A dermoscopic close-up of a skin lesion · a male patient, in their 80s — 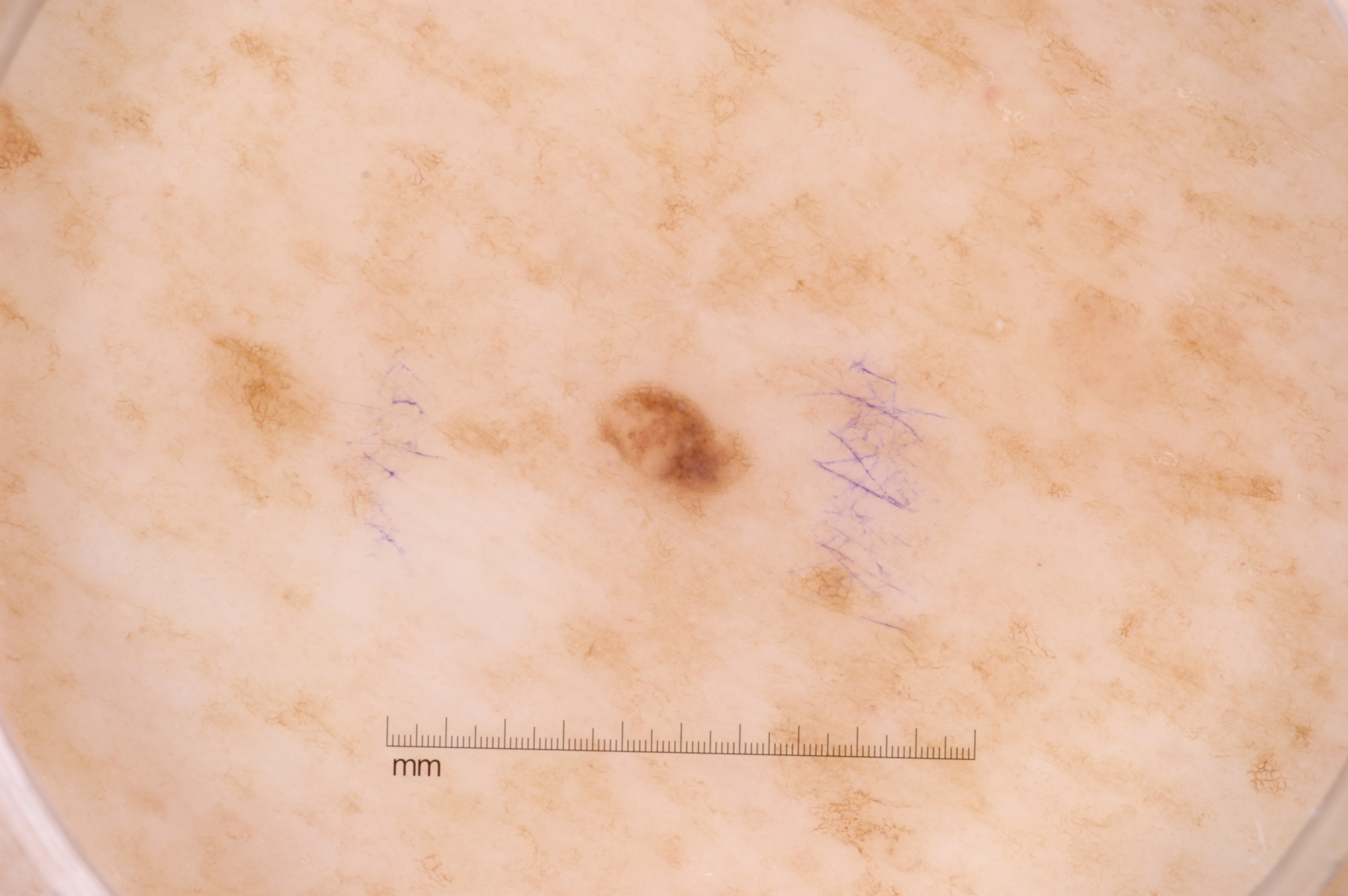A small lesion occupying a minor part of the field.
The lesion is bounded by left=590, top=379, right=757, bottom=527.
Dermoscopy demonstrates pigment network, with no streaks, milia-like cysts, or negative network.
Clinically diagnosed as a melanocytic nevus, a benign lesion.